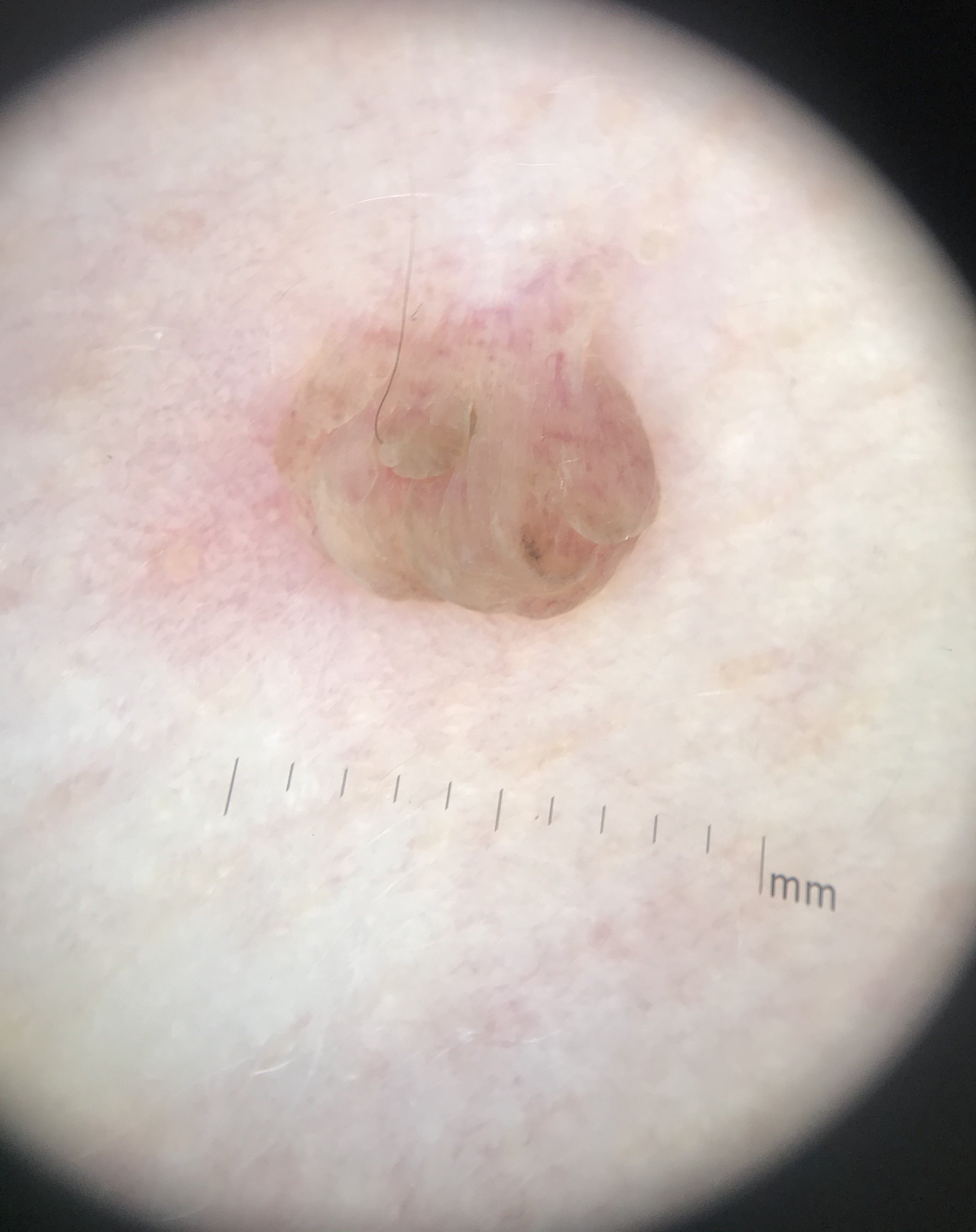A skin lesion imaged with a dermatoscope. The morphology is that of a banal lesion. Diagnosed as a dermal nevus.